A skin lesion imaged with a dermatoscope; a female subject aged 28 to 32:
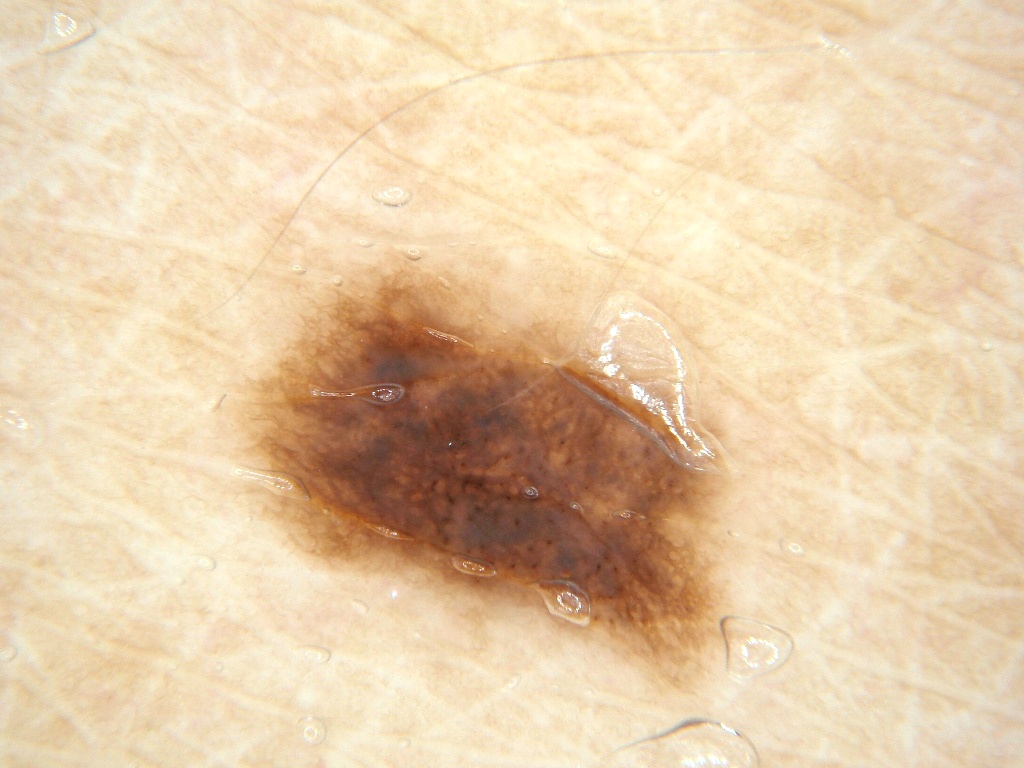size: moderate | lesion location: x1=249 y1=261 x2=728 y2=685 | features: pigment network | impression: a melanocytic nevus, a benign skin lesion.